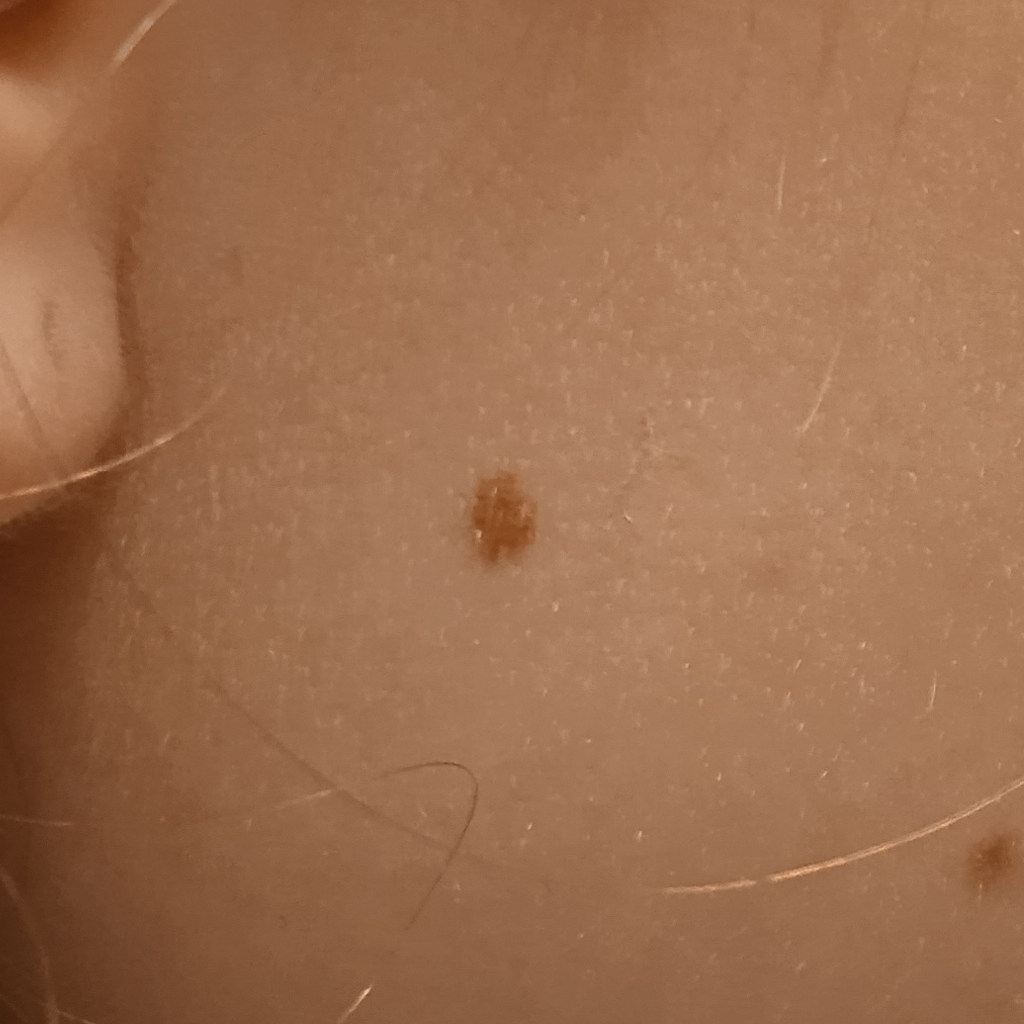A female subject aged 15. A clinical photograph of a skin lesion. Imaged for a research study, with no referral diagnosis recorded. Located on the face. Measuring roughly 3.6 mm. The diagnostic impression was a melanocytic nevus.